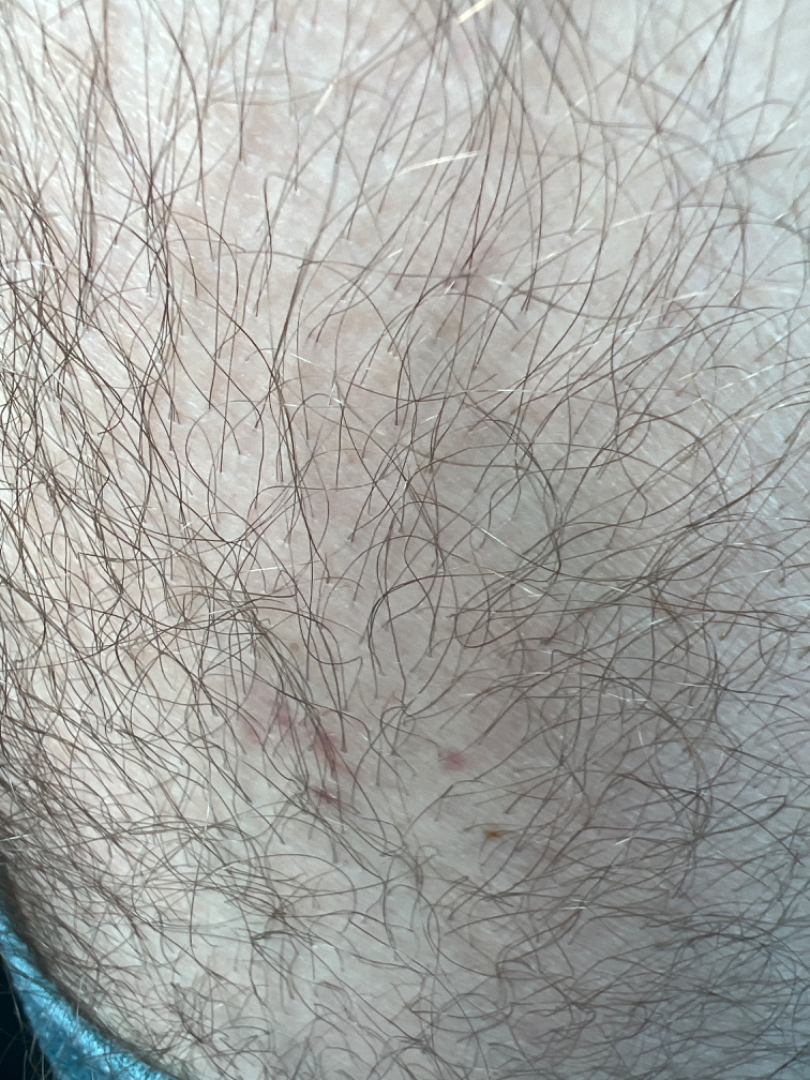The case was indeterminate on photographic review. The photograph was taken at an angle. The affected area is the leg.